The patient is Fitzpatrick III; a female subject 70 years old; a clinical photo of a skin lesion taken with a smartphone: 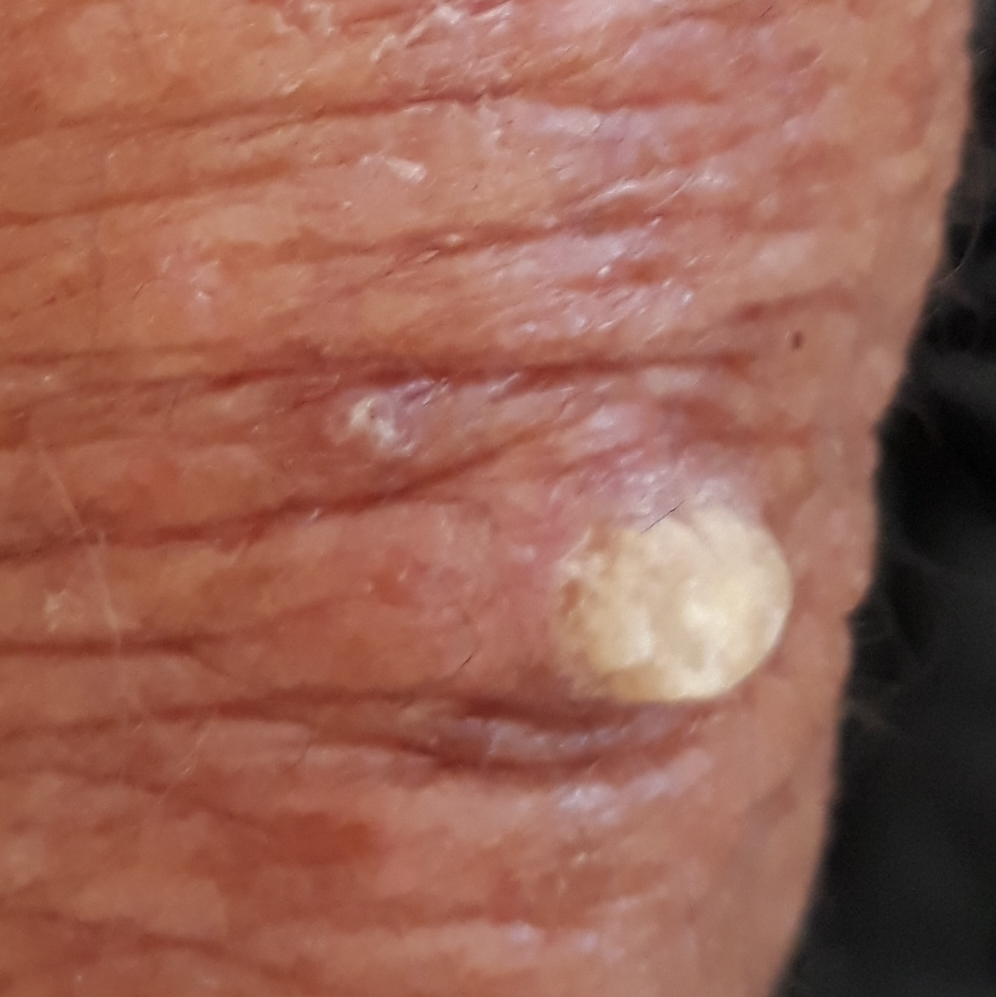Located on an arm.
Measuring about 10 × 6 mm.
Per patient report, the lesion hurts, has changed, is elevated, and has grown, but does not itch.
Histopathological examination showed an actinic keratosis.